A close-up photograph · located on the front of the torso and back of the torso · present for more than one year: 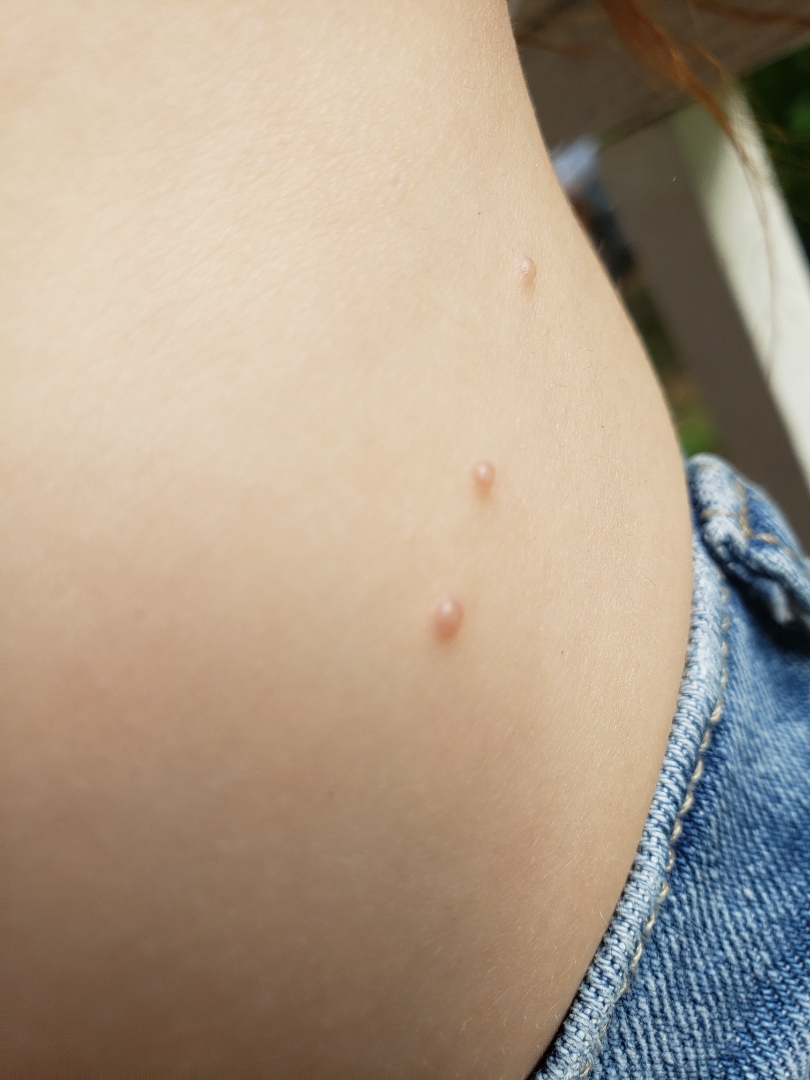The impression is Molluscum Contagiosum.